This image was taken at an angle:
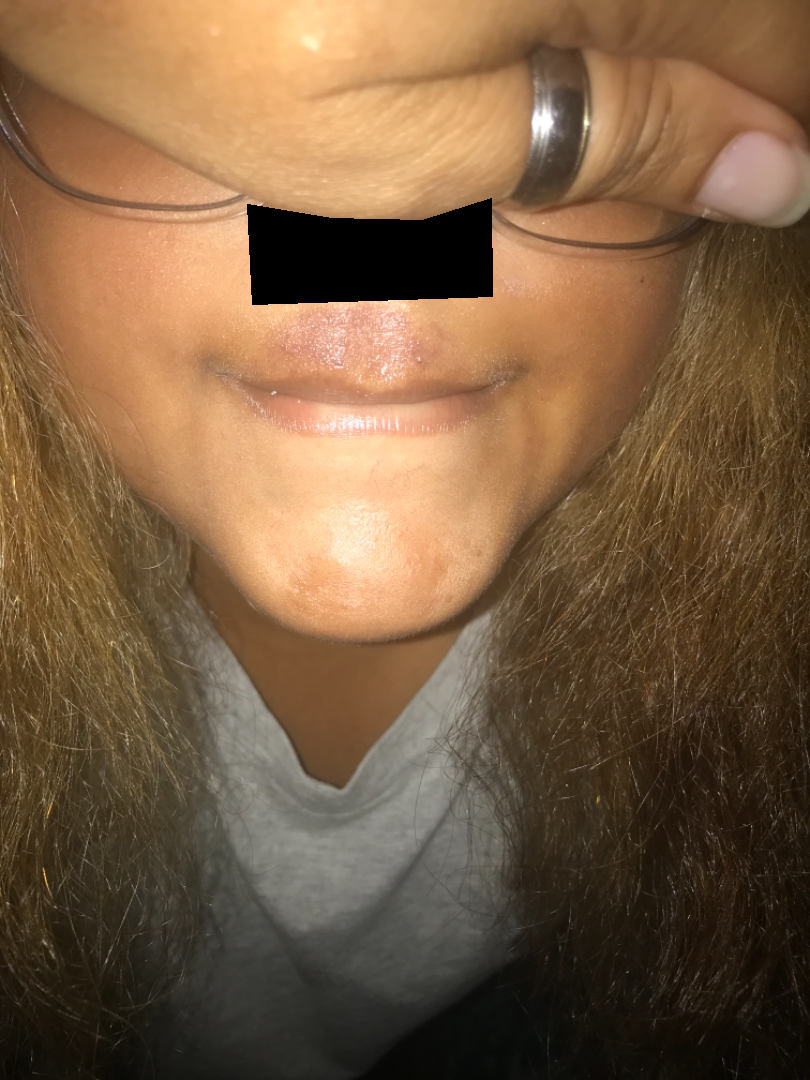differential diagnosis — the primary impression is Irritant Contact Dermatitis; with consideration of Allergic Contact Dermatitis.